The chart documents a previous melanoma; a dermoscopic image of a skin lesion — 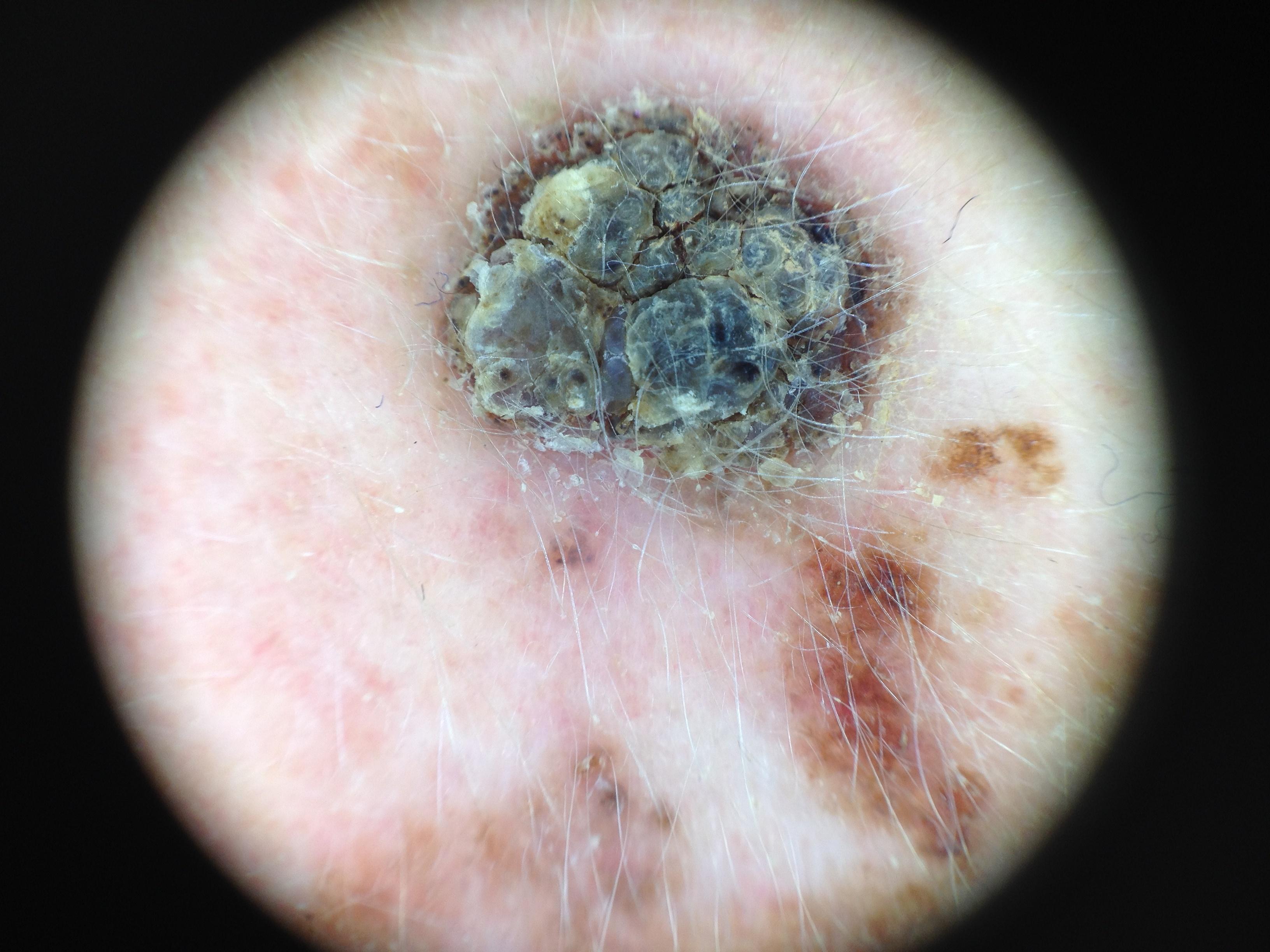Q: What is the anatomic site?
A: the head or neck
Q: What is this lesion?
A: Melanoma (biopsy-proven)